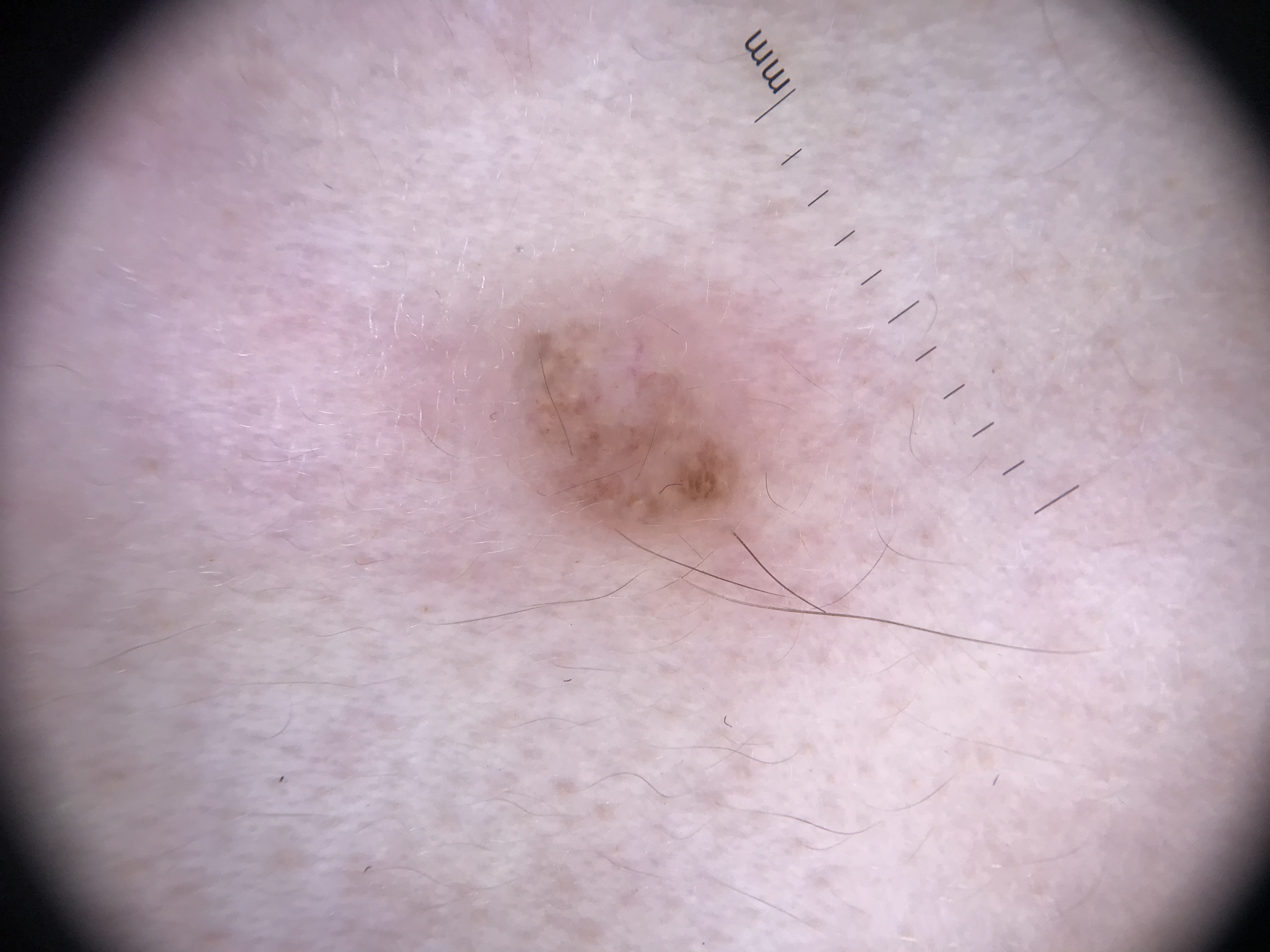– image: dermatoscopy
– label: dermal nevus (expert consensus)